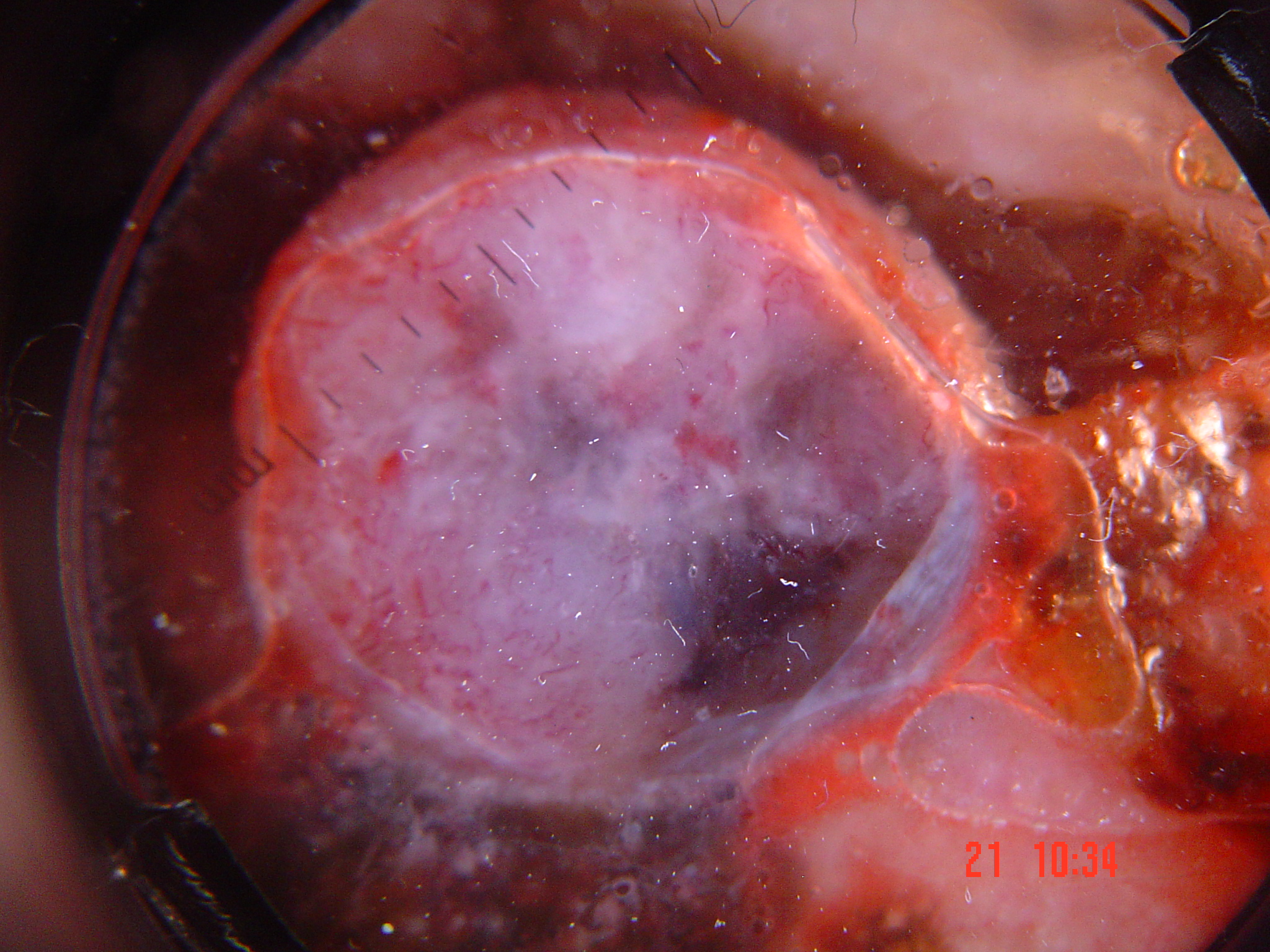image type = dermatoscopy, diagnosis = lentigo maligna melanoma (biopsy-proven).